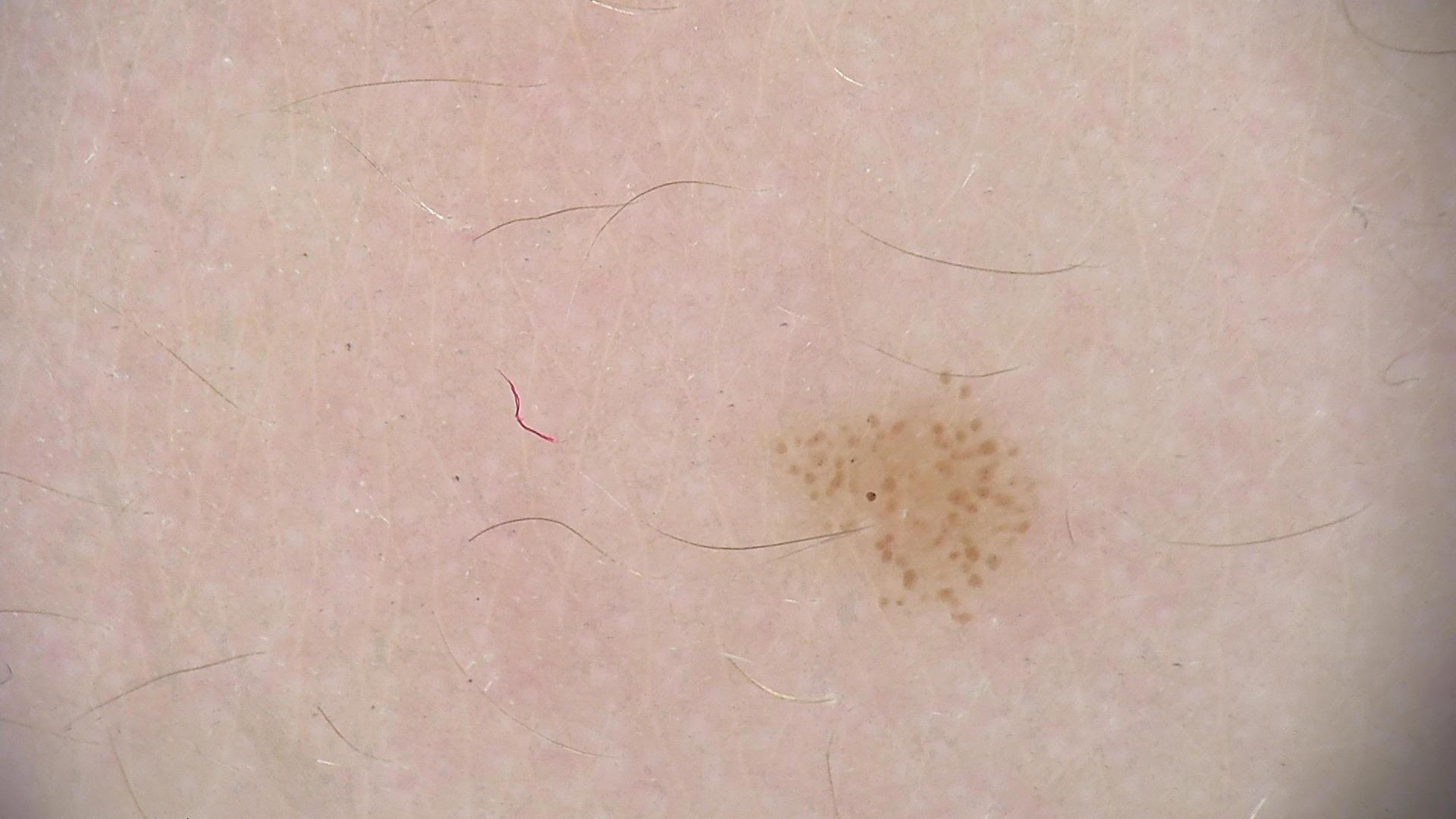{"image": "dermoscopy", "diagnosis": {"name": "dysplastic junctional nevus", "code": "jd", "malignancy": "benign", "super_class": "melanocytic", "confirmation": "expert consensus"}}